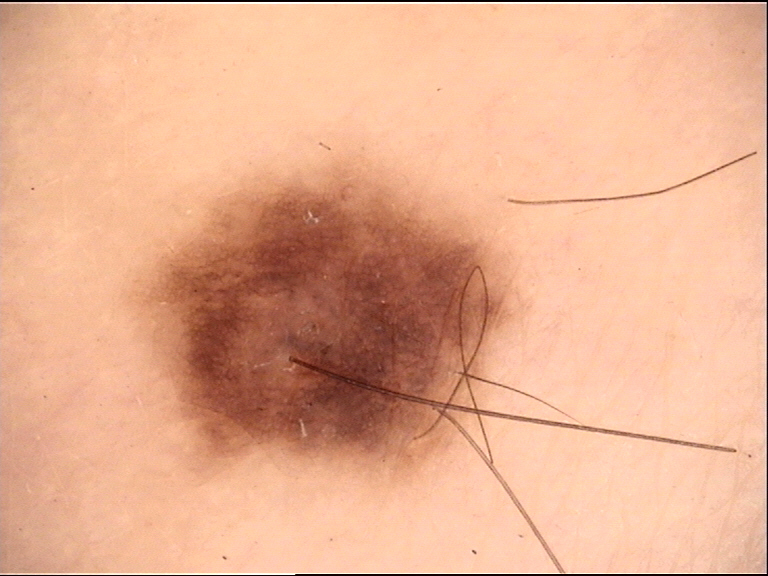Findings:
A skin lesion imaged with a dermatoscope.
Conclusion:
Labeled as a banal lesion — a compound nevus.